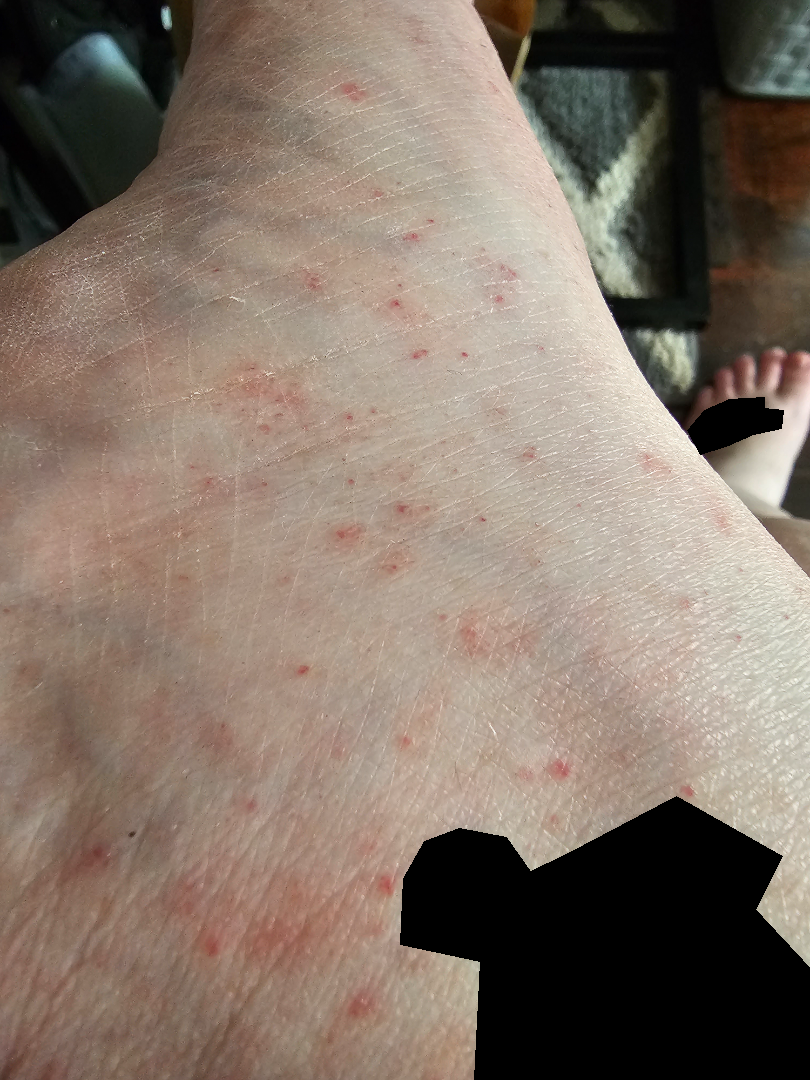Impression: Single-reviewer assessment: the differential is split between Pigmented purpuric eruption and Leukocytoclastic Vasculitis.